Located on the arm and back of the hand; the photo was captured at an angle.
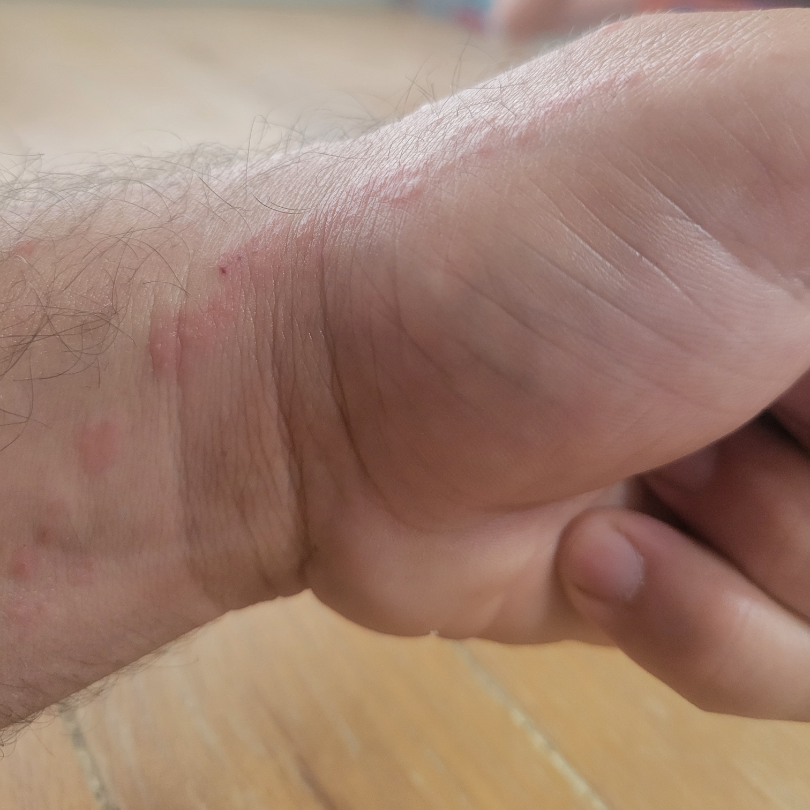assessment=could not be assessed.